A skin lesion imaged with a dermatoscope:
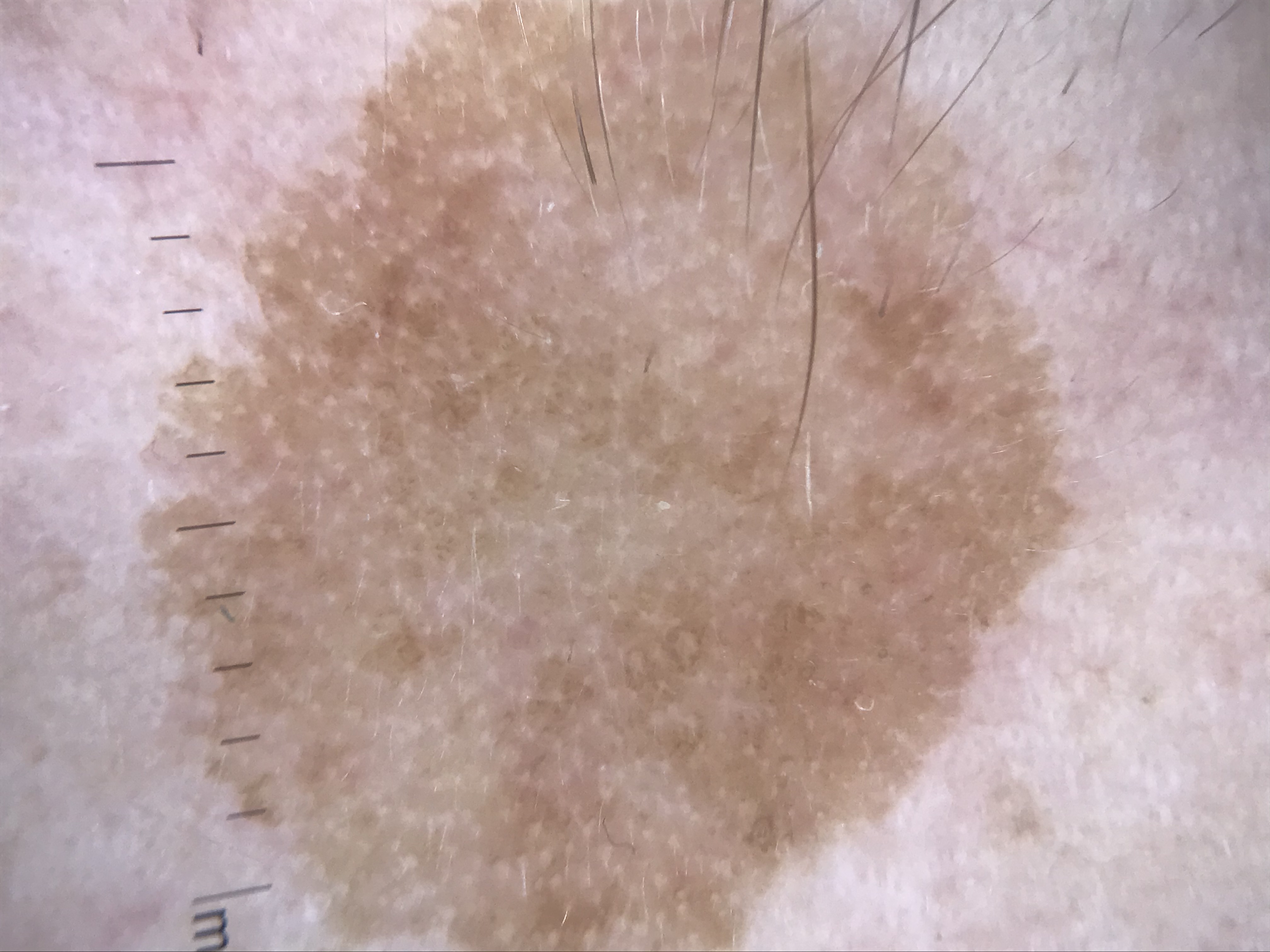The diagnosis was a keratinocytic lesion — a seborrheic keratosis.